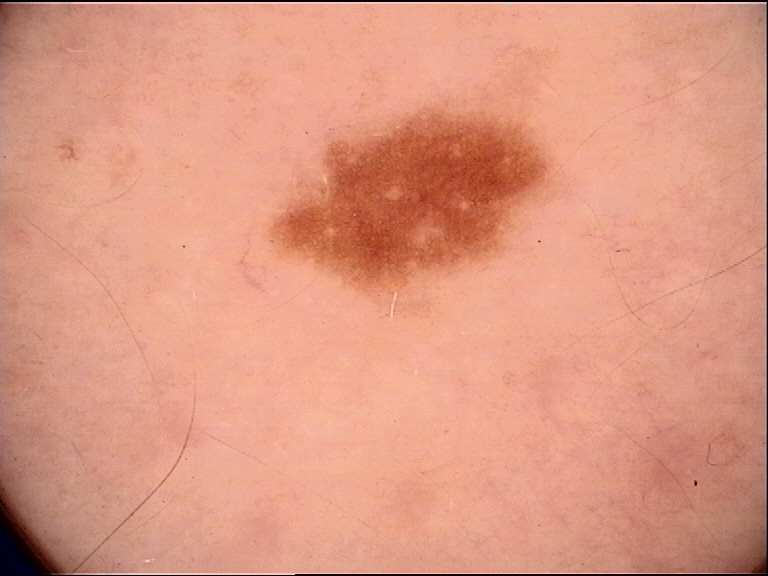Classified as a dysplastic junctional nevus.